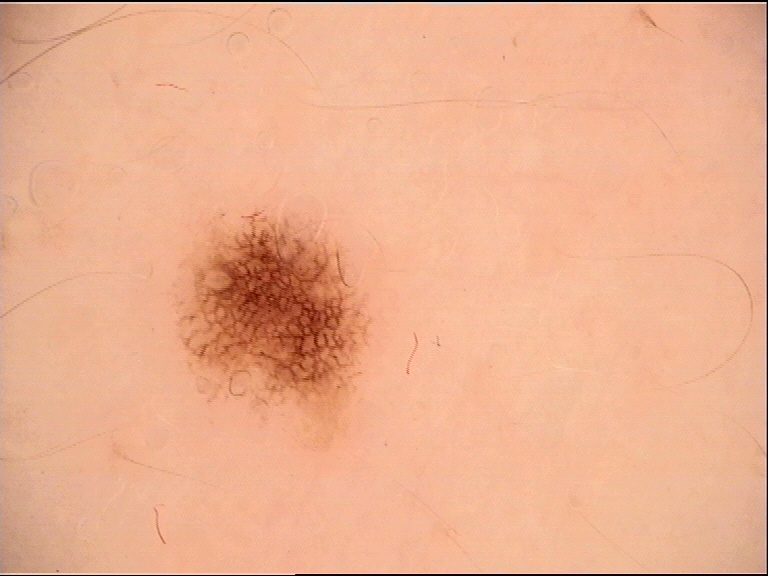Q: What kind of image is this?
A: dermoscopy
Q: What is the diagnosis?
A: dysplastic junctional nevus (expert consensus)